Collected as part of a research study, without a referral diagnosis · a male patient 77 years of age · a clinical close-up of a skin lesion — 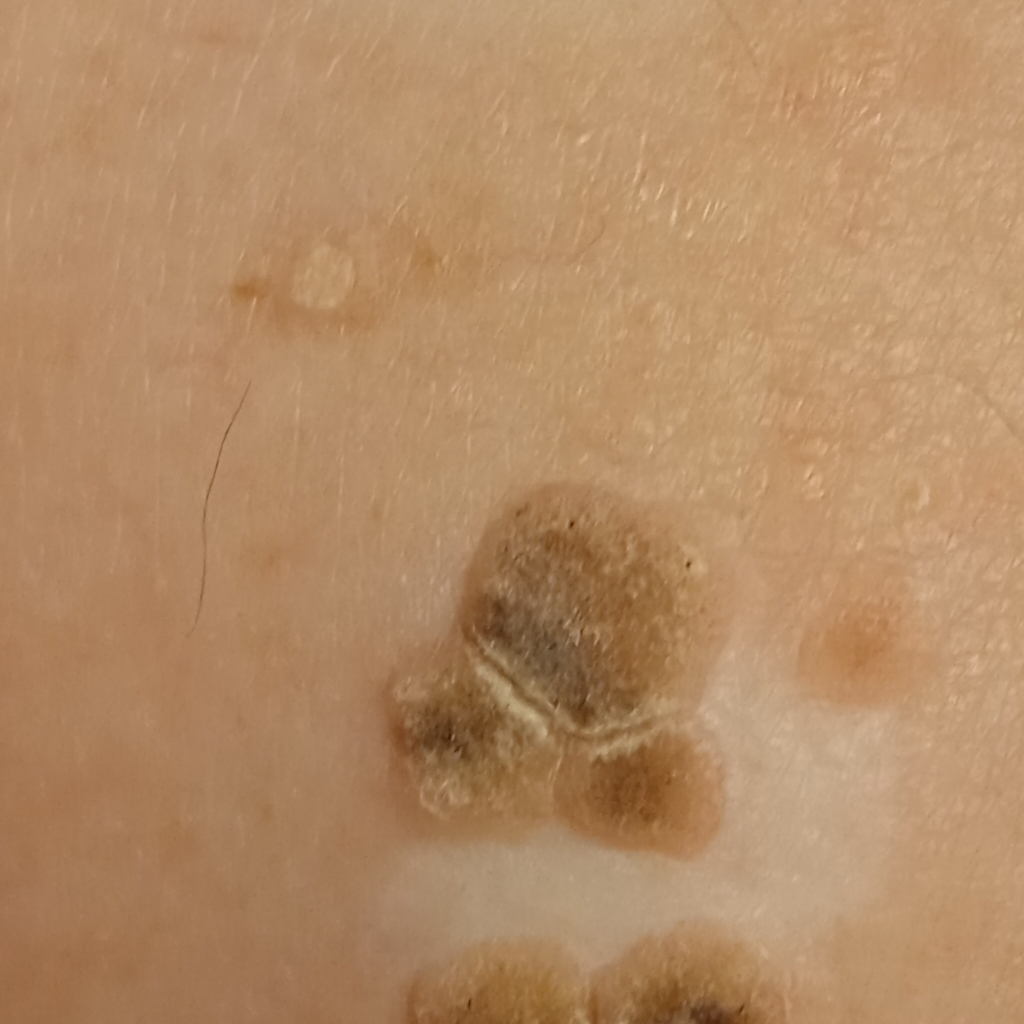Located on the back.
The lesion measures approximately 14.2 mm.
The dermatologists' assessment was a seborrheic keratosis.